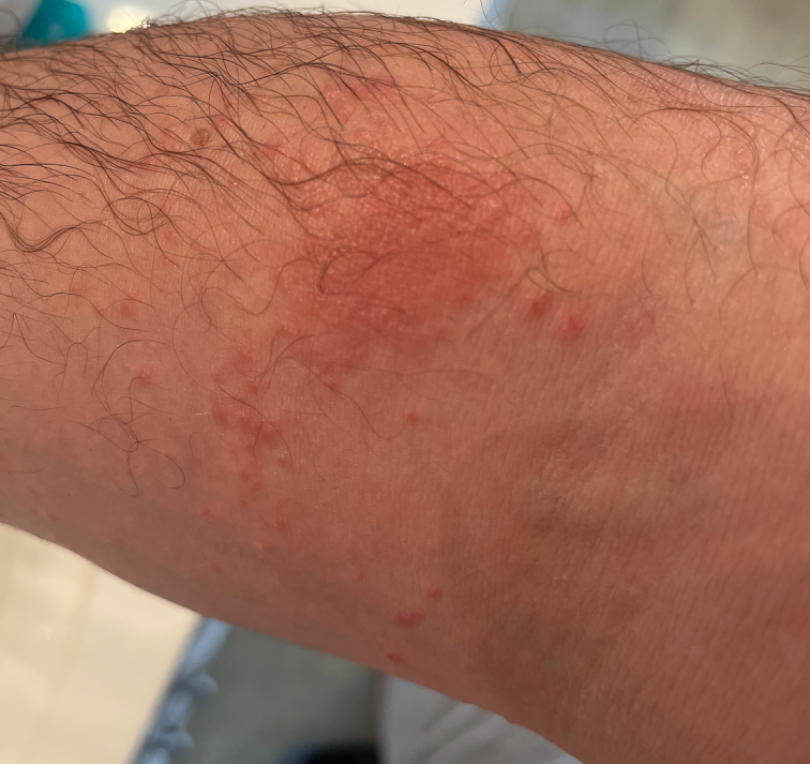Impression:
One reviewing dermatologist: favoring Allergic Contact Dermatitis; with consideration of Irritant Contact Dermatitis; less likely is Urticaria.